Per the chart, a prior melanoma; a male subject about 85 years old or older — 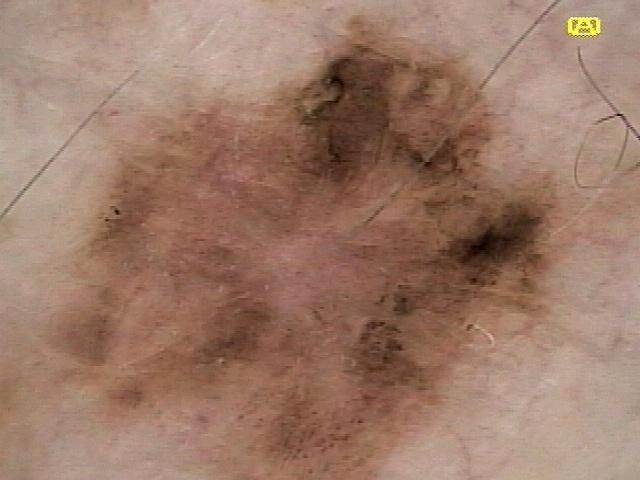diagnostic label=Melanoma (biopsy-proven).